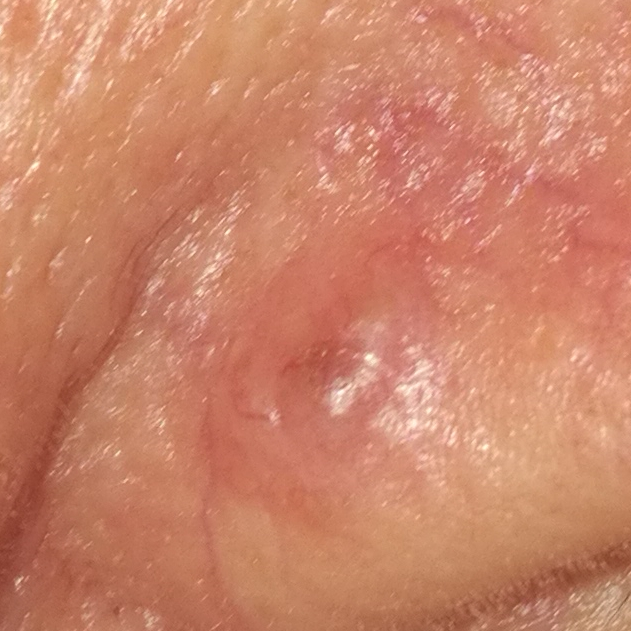subject: female, 71 years old
risk factors: prior malignancy (patient or family)
image: clinical photo
FST: II
lesion size: 7 × 6 mm
reported symptoms: elevation, itching
pathology: basal cell carcinoma (biopsy-proven)